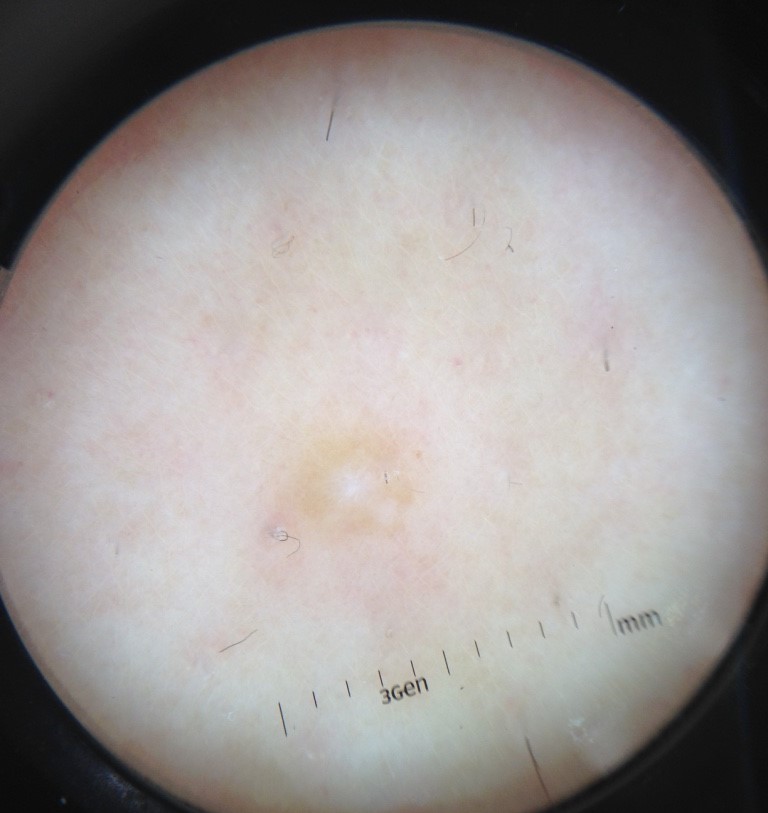Findings:
* modality: dermoscopy
* class: dermatofibroma (expert consensus)